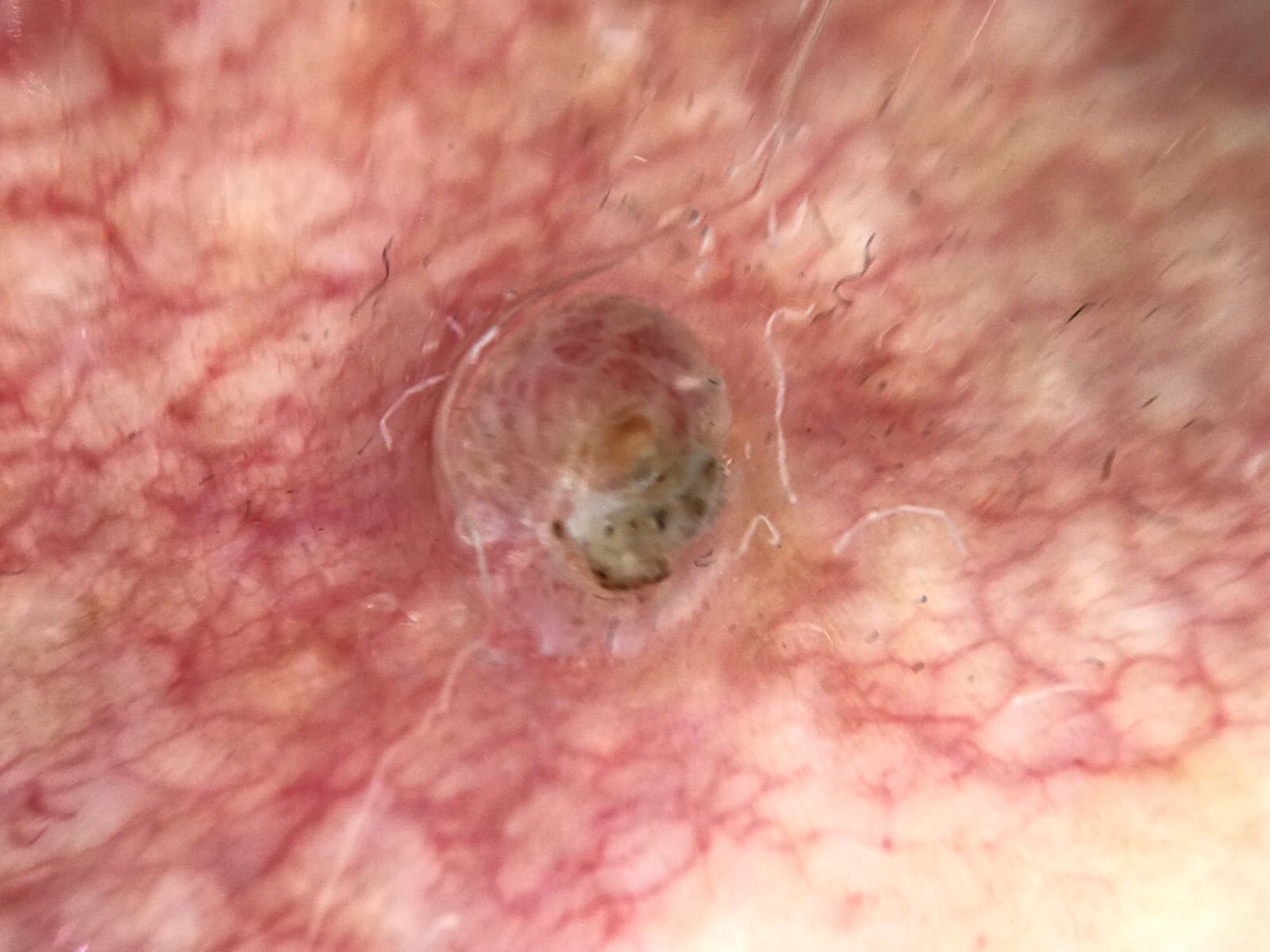Case:
* imaging — dermoscopy
* class — squamous cell carcinoma (biopsy-proven)